This is a close-up image: 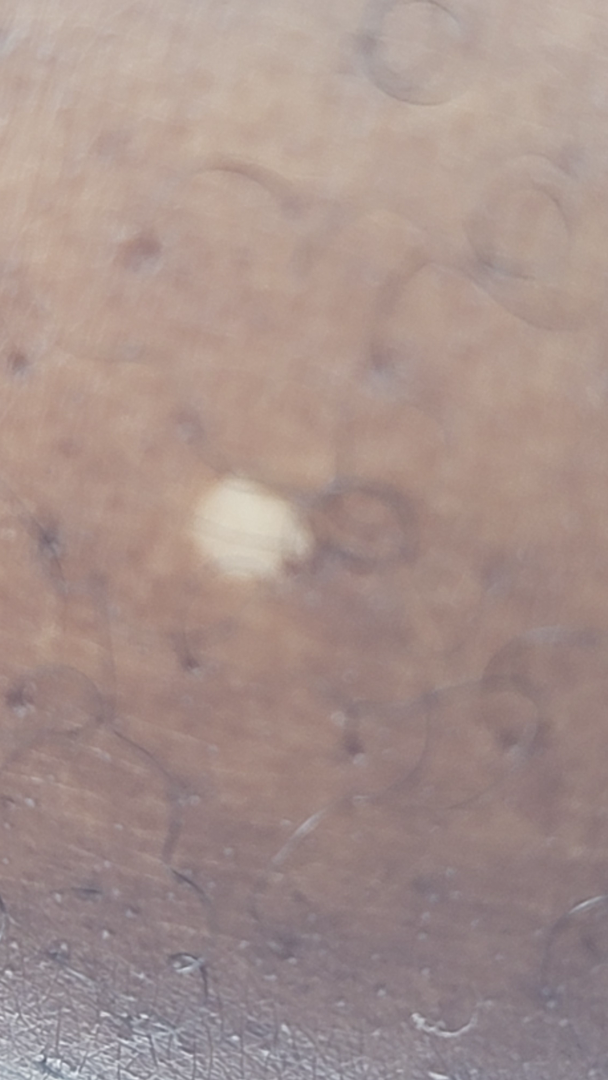The dermatologist could not determine a likely condition from the photograph alone.